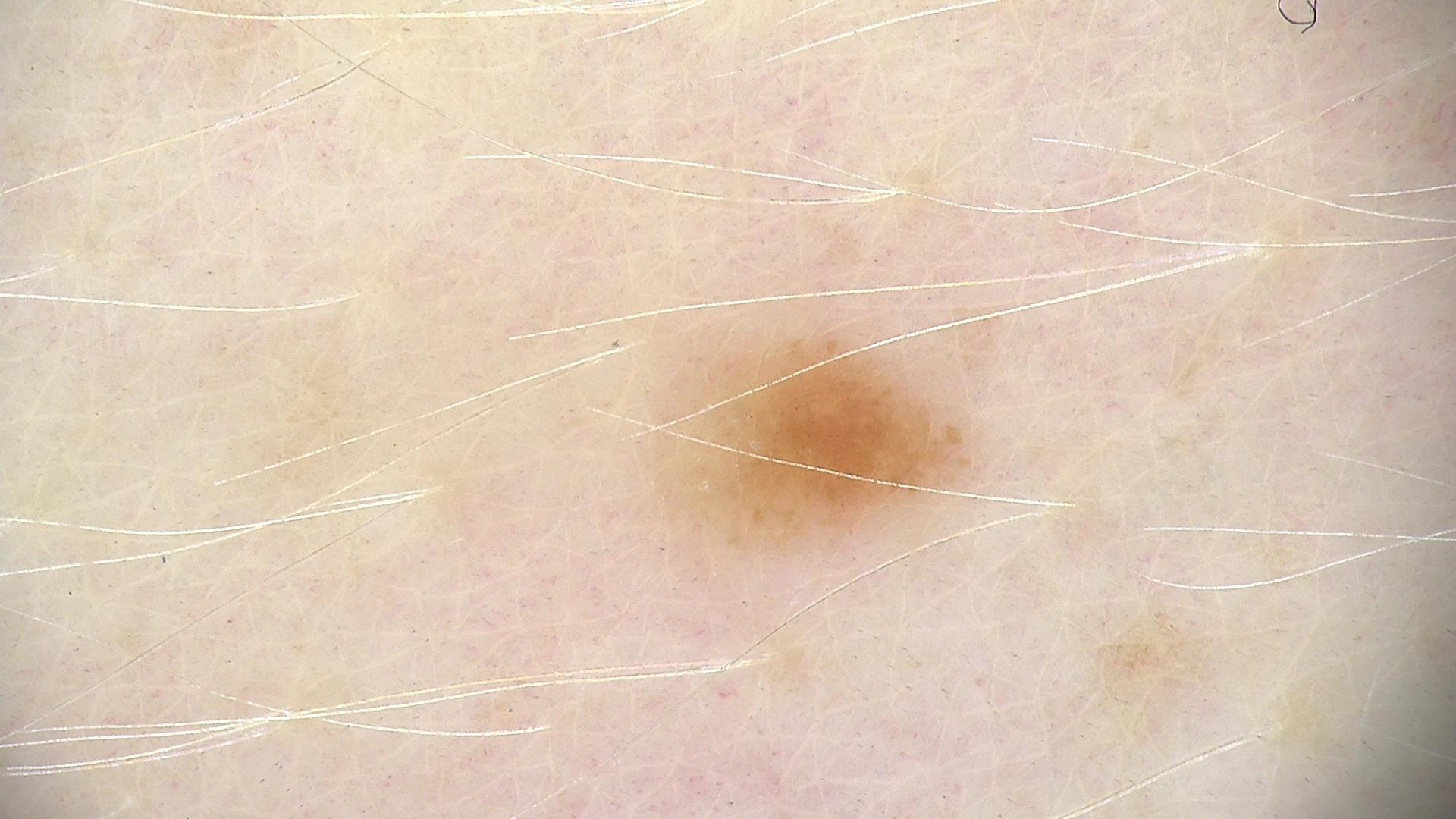Case:
A dermoscopic photograph of a skin lesion.
Impression:
Classified as a banal lesion — a junctional nevus.